A dermoscopy image of a single skin lesion:
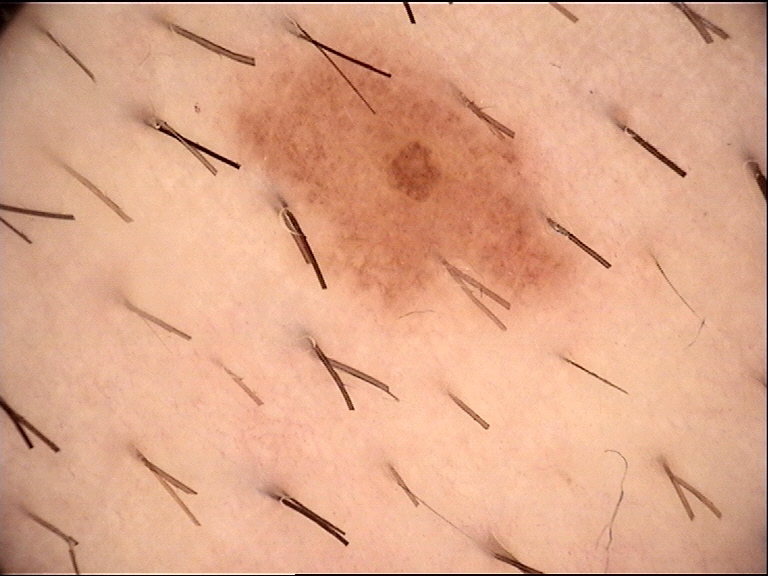The diagnostic label was a benign lesion — a dysplastic junctional nevus.